A female subject in their mid- to late 20s; the patient is Fitzpatrick II; a dermoscopic photograph of a skin lesion.
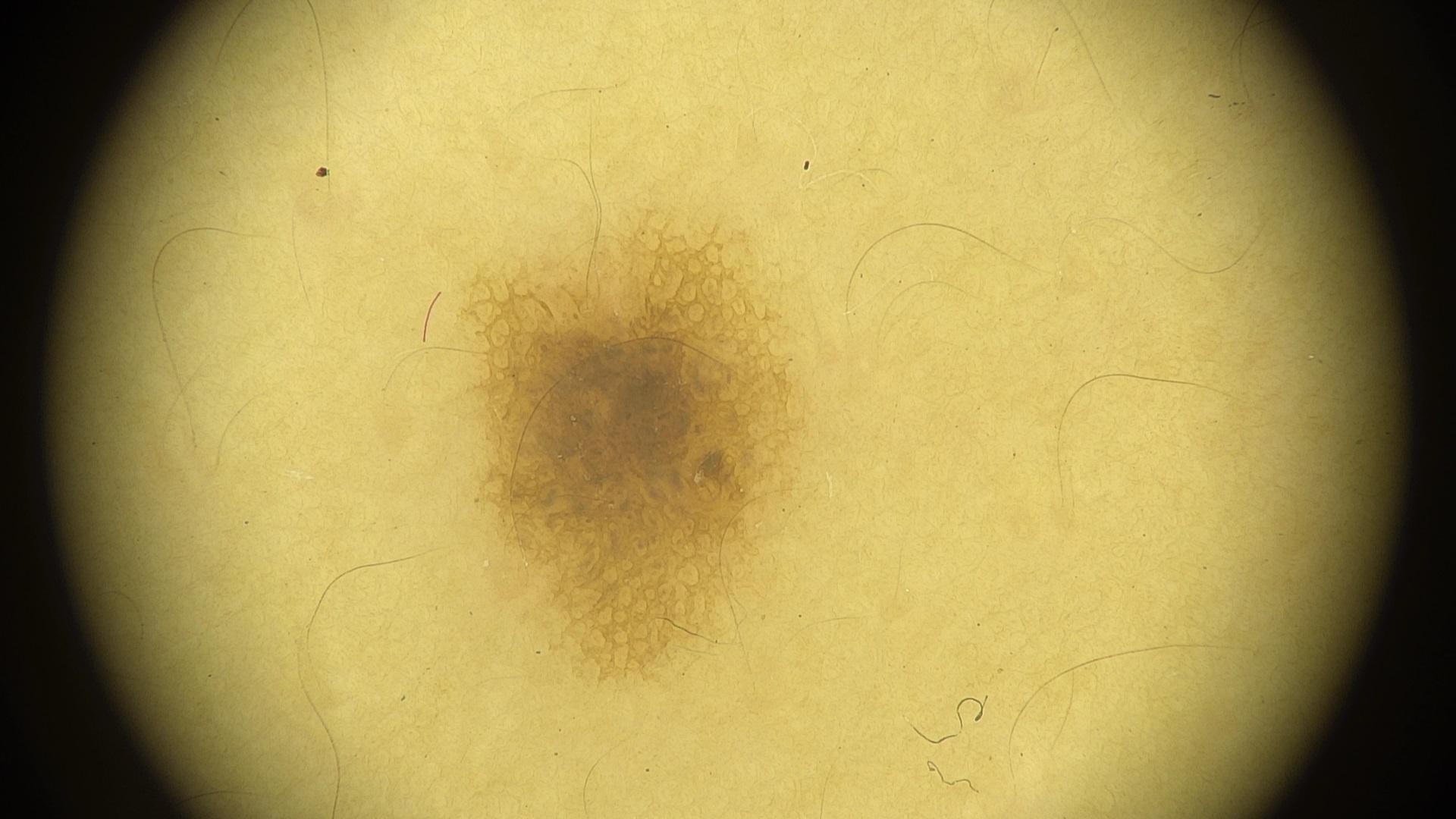Q: Where on the body is the lesion?
A: the trunk
Q: What is the diagnosis?
A: Nevus (clinical impression)